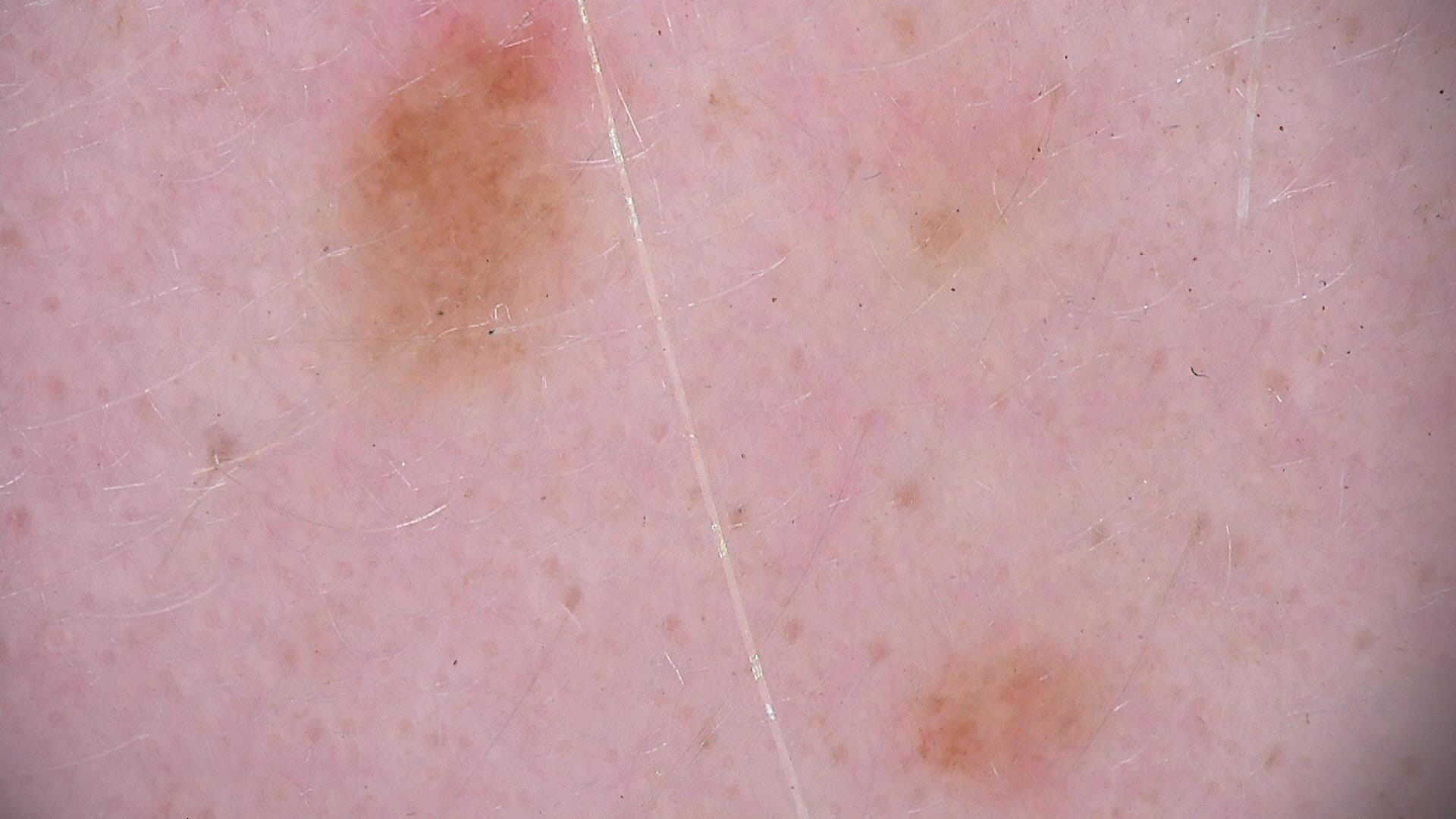Impression:
Labeled as a dysplastic junctional nevus.